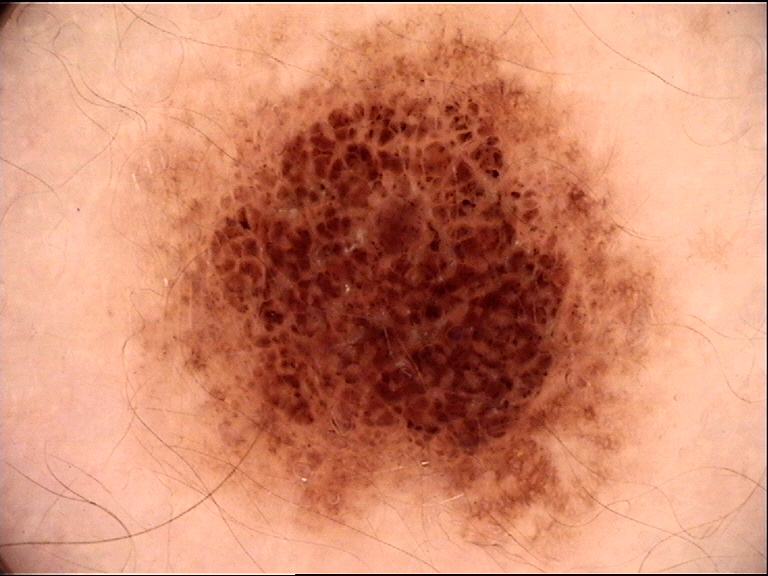The diagnosis was a dysplastic junctional nevus.